A dermoscopic close-up of a skin lesion.
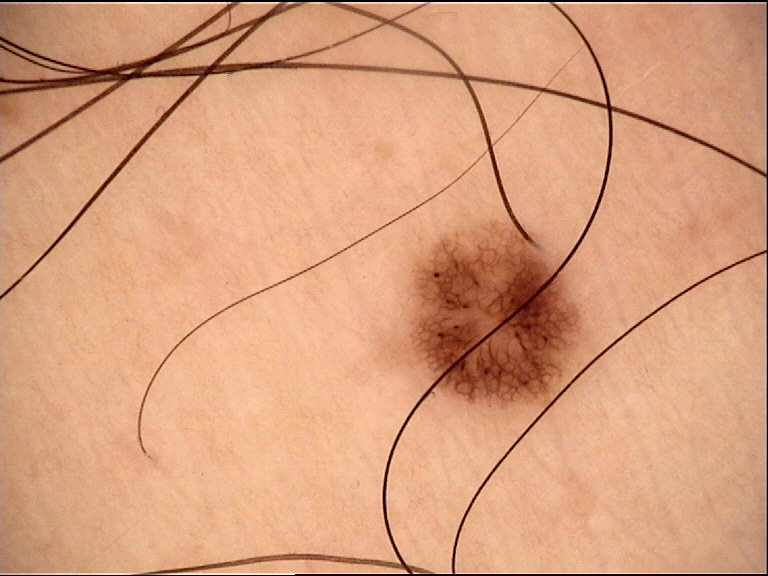Classified as a dysplastic junctional nevus.